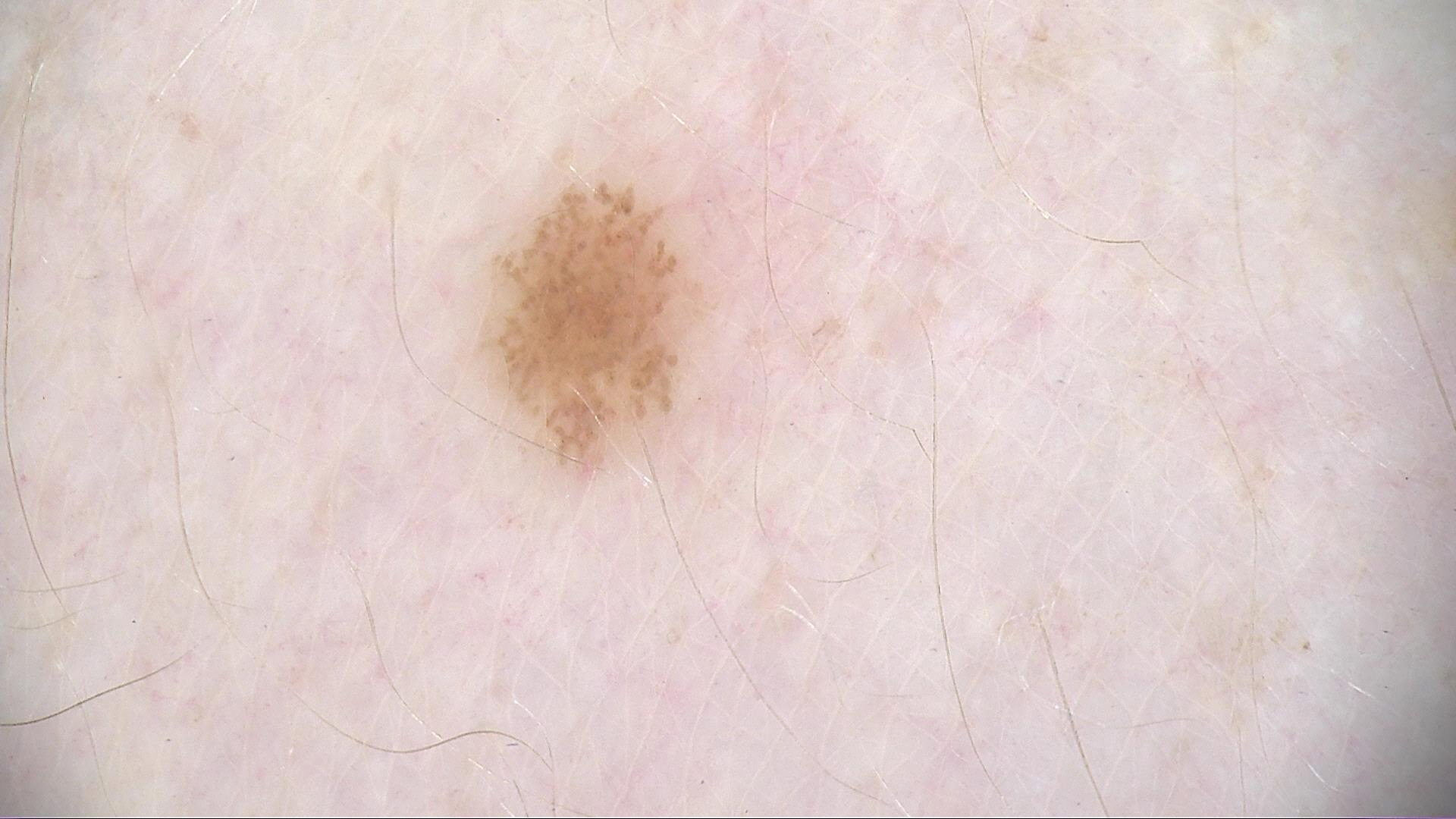modality: dermoscopy | diagnosis: dysplastic junctional nevus (expert consensus).